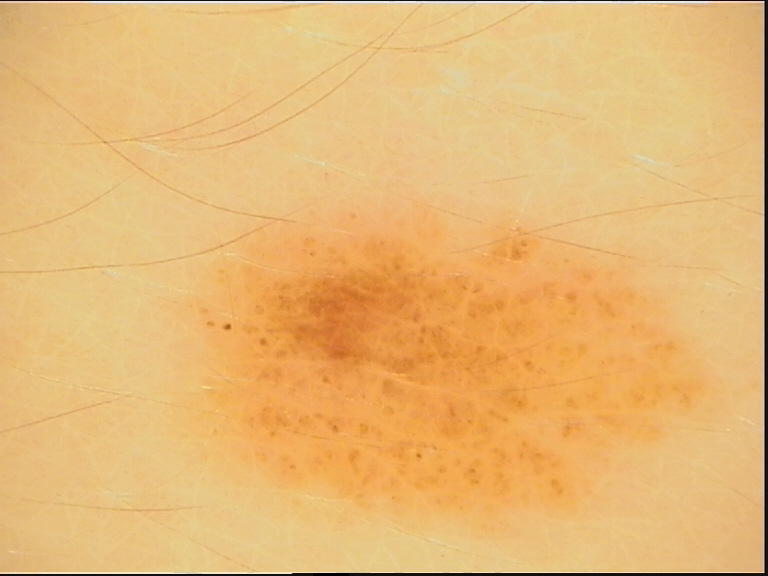Summary: A dermoscopic close-up of a skin lesion. Conclusion: Classified as a banal lesion — a junctional nevus.